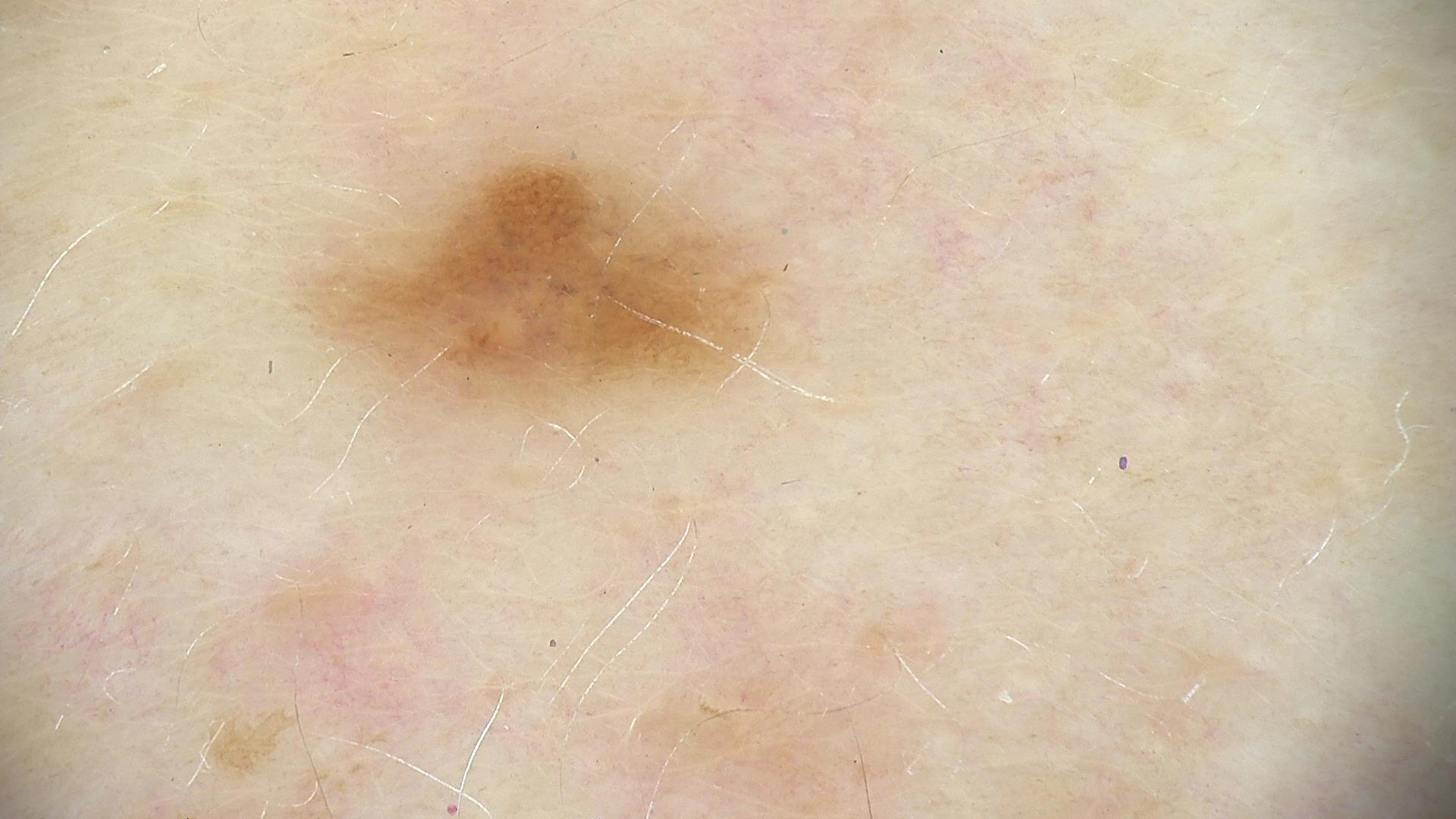The diagnostic label was a dysplastic junctional nevus.